A male patient aged 53-57 · a dermoscopic close-up of a skin lesion · skin type II.
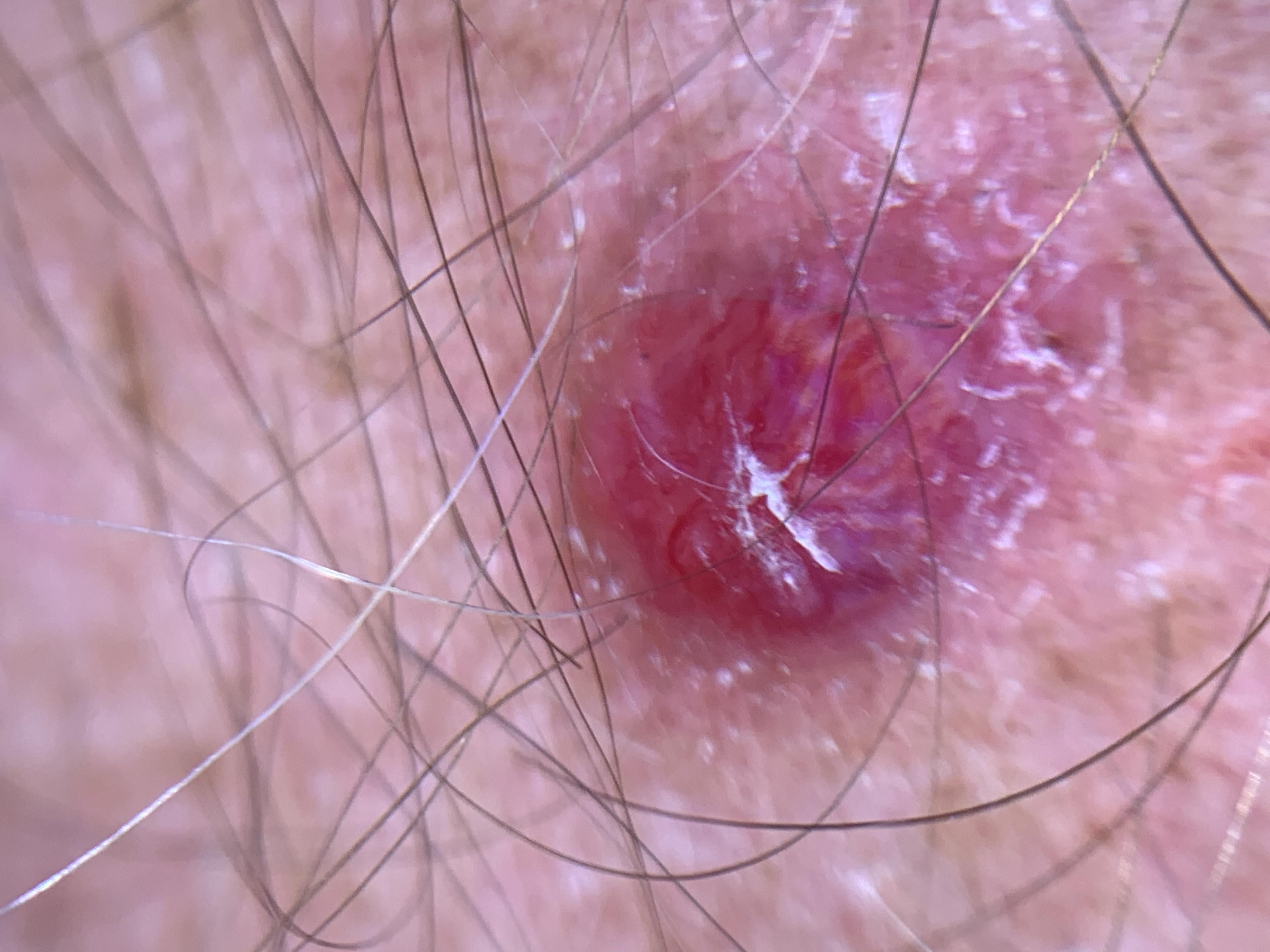Conclusion: Histopathology confirmed an adnexal lesion — a basal cell carcinoma.